A subject 77 years of age: 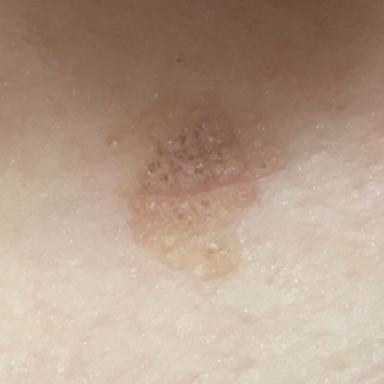Located on the chest. The patient reports no symptoms. Consistent with a seborrheic keratosis.